A wide-field clinical photograph of a skin lesion — 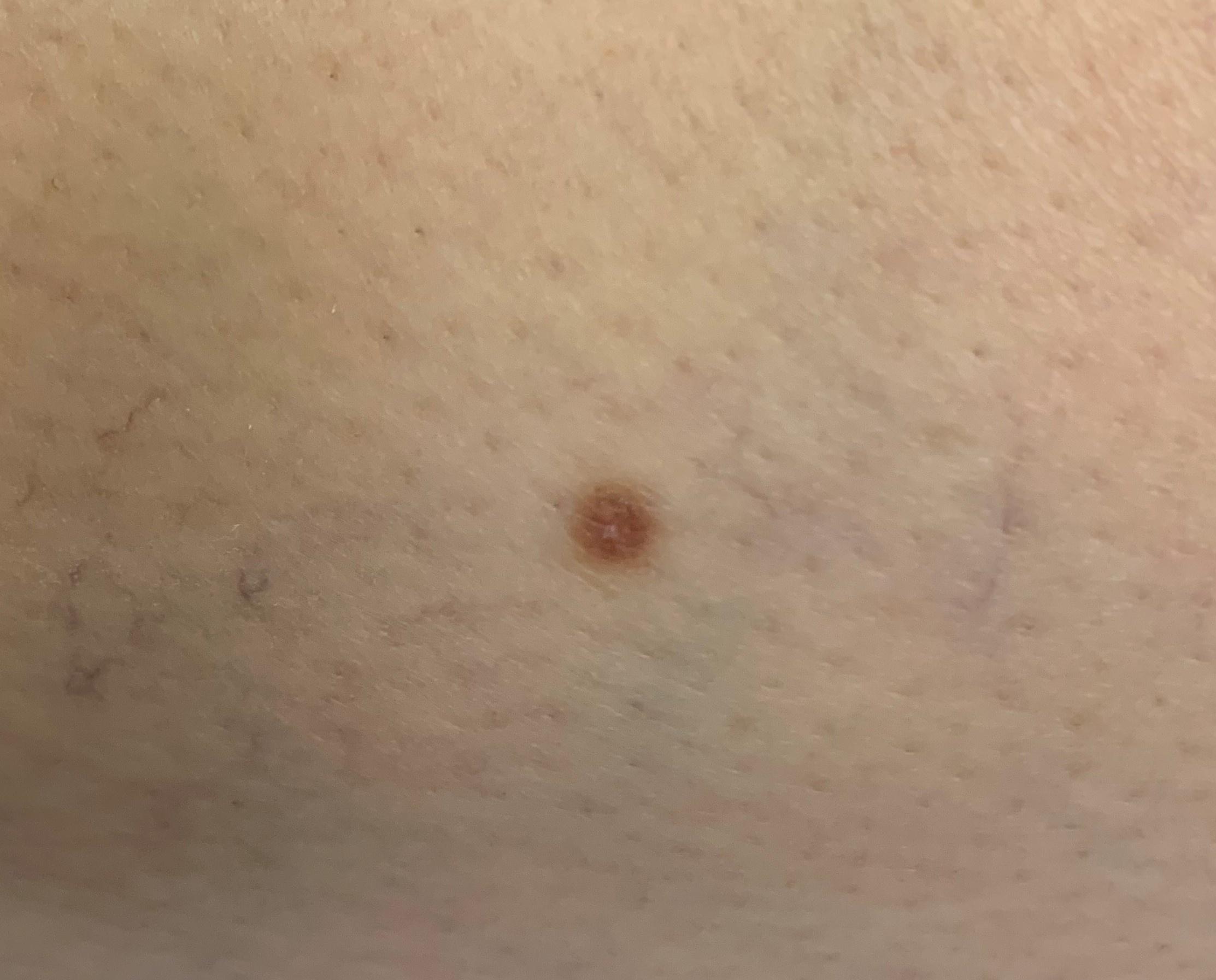* impression · Dermatofibroma